A clinical photograph showing a skin lesion · a male subject in their early teens:
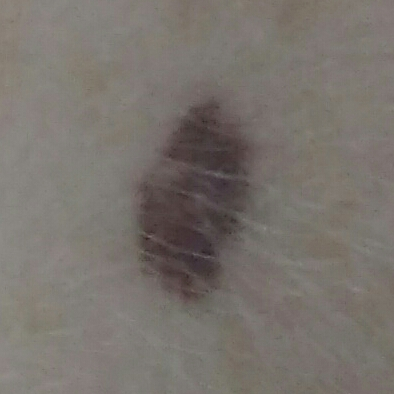The lesion is on the face. The biopsy diagnosis was a nevus.